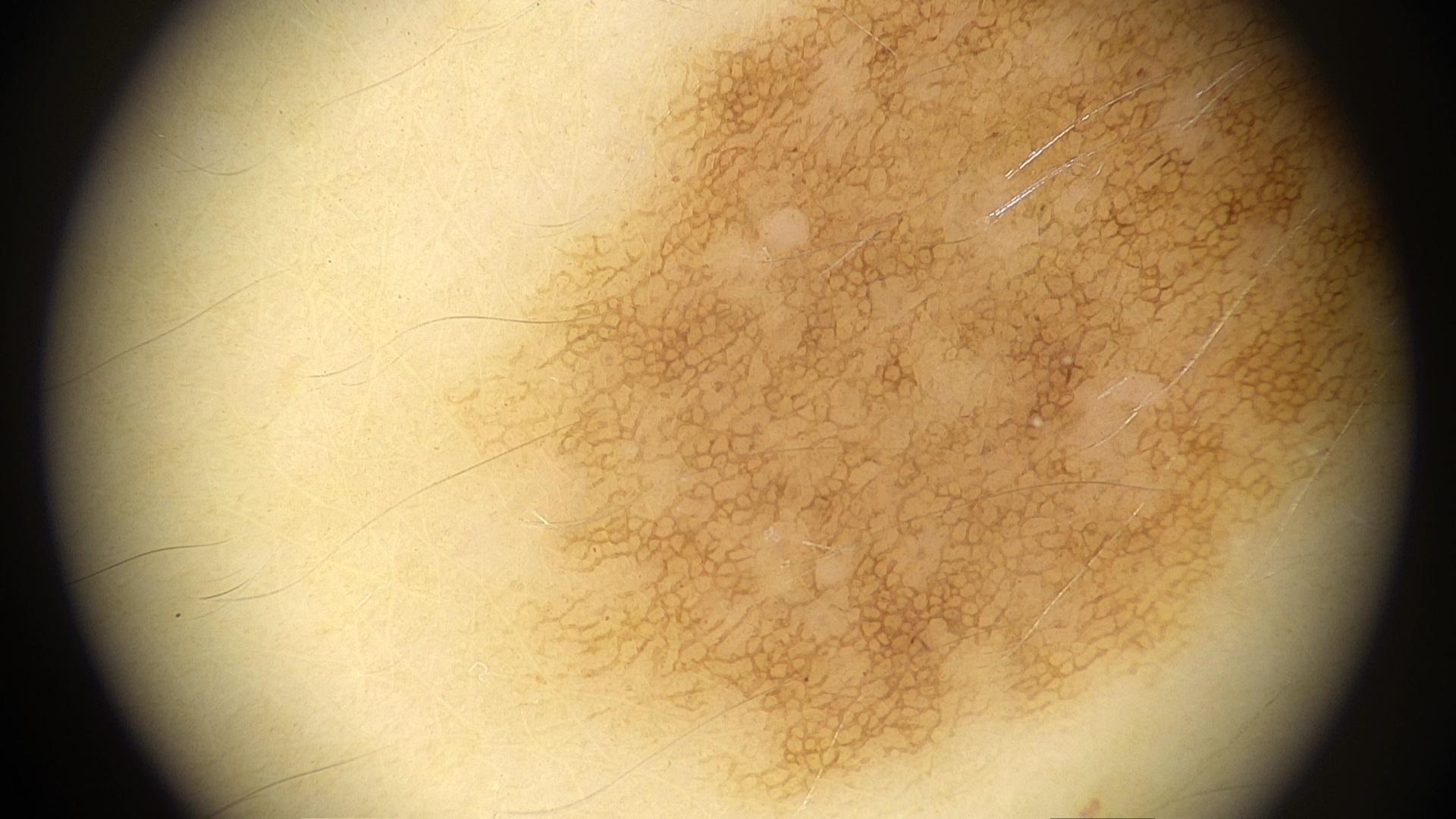Q: What are the patient's age and sex?
A: female, aged approximately 35
Q: What kind of image is this?
A: contact-polarized dermoscopy
Q: What is the anatomic site?
A: the trunk, specifically the posterior trunk
Q: What is the diagnosis?
A: Nevus